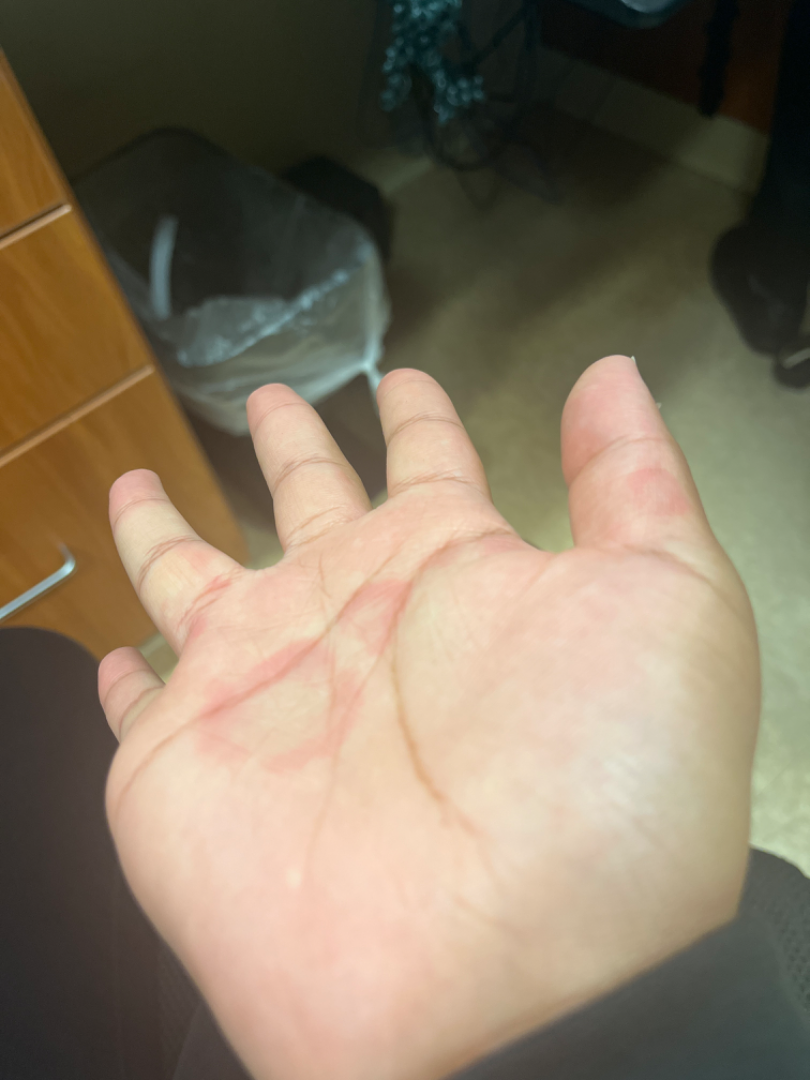<summary>
  <shot_type>at an angle</shot_type>
  <patient>female, age 18–29</patient>
  <body_site>palm</body_site>
  <differential>
    <leading>Urticaria</leading>
    <unlikely>Drug Rash, Erythema multiforme, Geographic tongue</unlikely>
  </differential>
</summary>